An image taken at an angle — 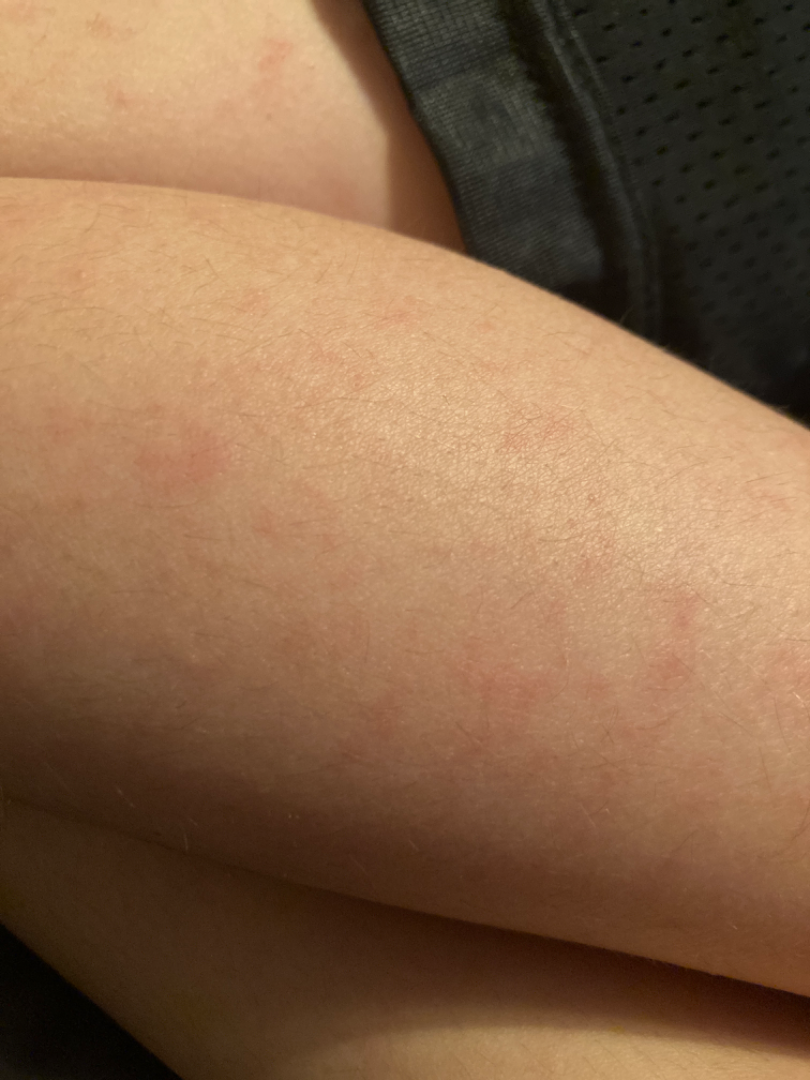The skin condition could not be confidently assessed from this image.